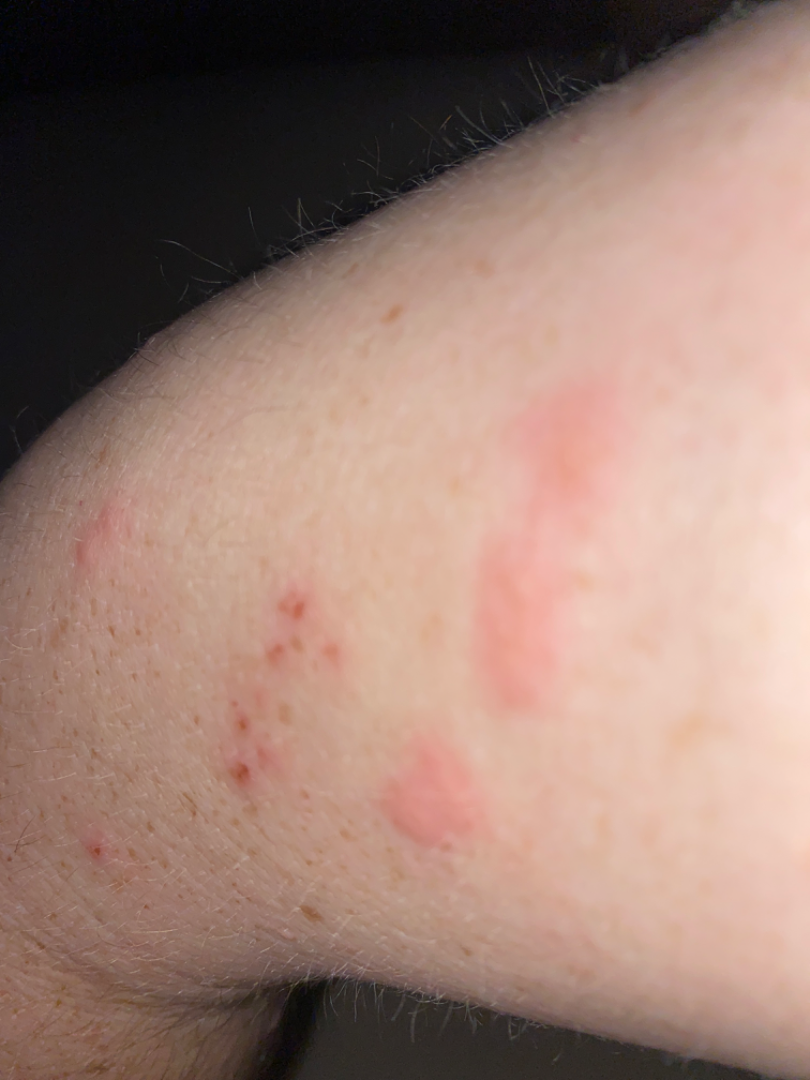Close-up view. On remote dermatologist review, Insect Bite and Inflicted skin lesions were considered with similar weight.